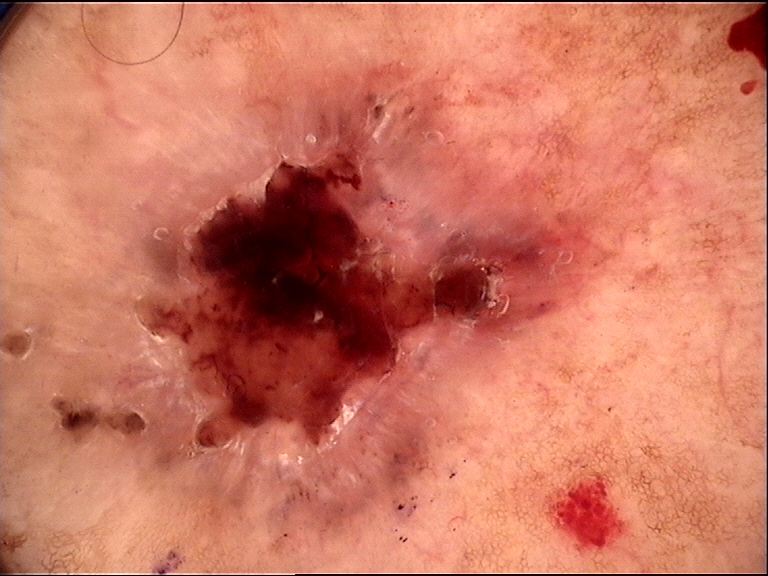| feature | finding |
|---|---|
| imaging | dermoscopy |
| subtype | keratinocytic |
| class | basal cell carcinoma (biopsy-proven) |